A dermoscopy image of a single skin lesion:
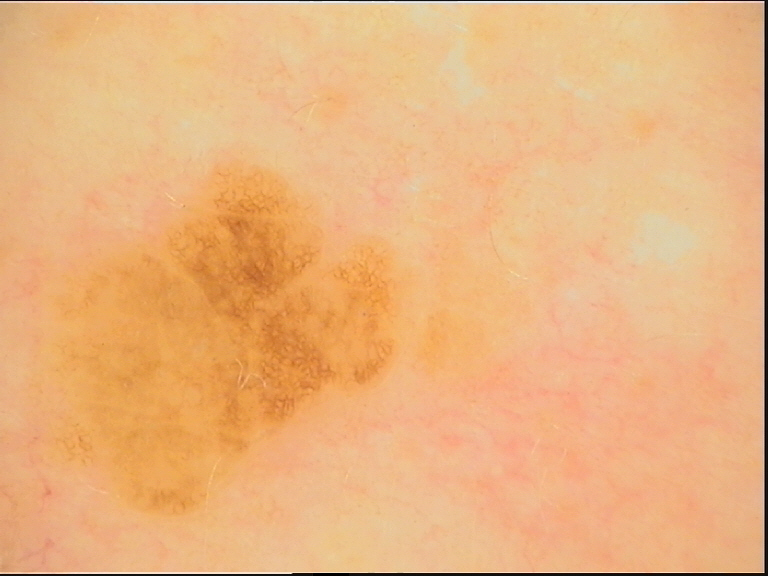Conclusion:
The diagnostic label was a banal lesion — a junctional nevus.